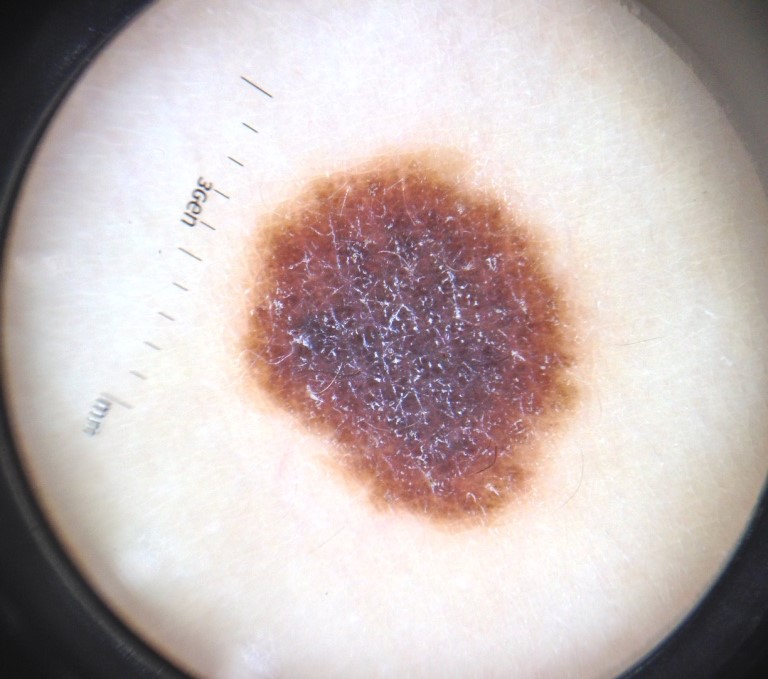A dermoscopic photograph of a skin lesion. Diagnosed as a congenital compound nevus.